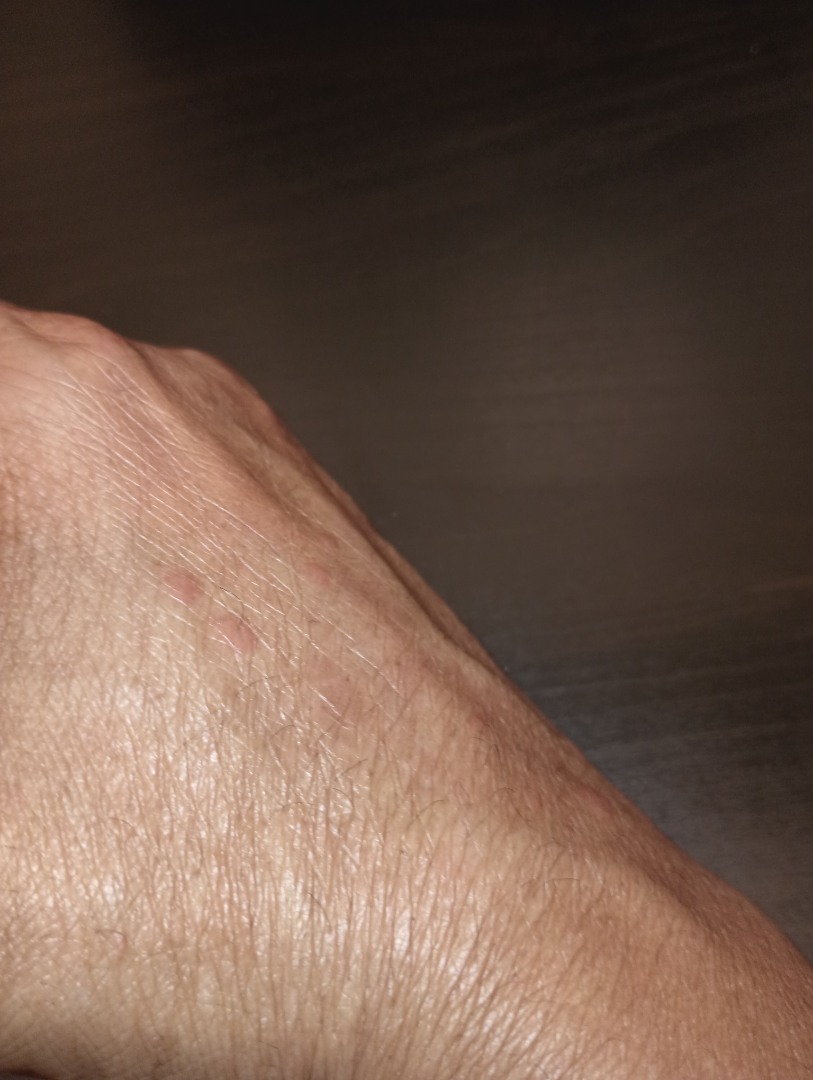Case summary:
- dermatologist impression · the differential, in no particular order, includes Granuloma annulare and Insect Bite; less likely is Verruca vulgaris; a remote consideration is Cutaneous sarcoidosis